This is a close-up image:
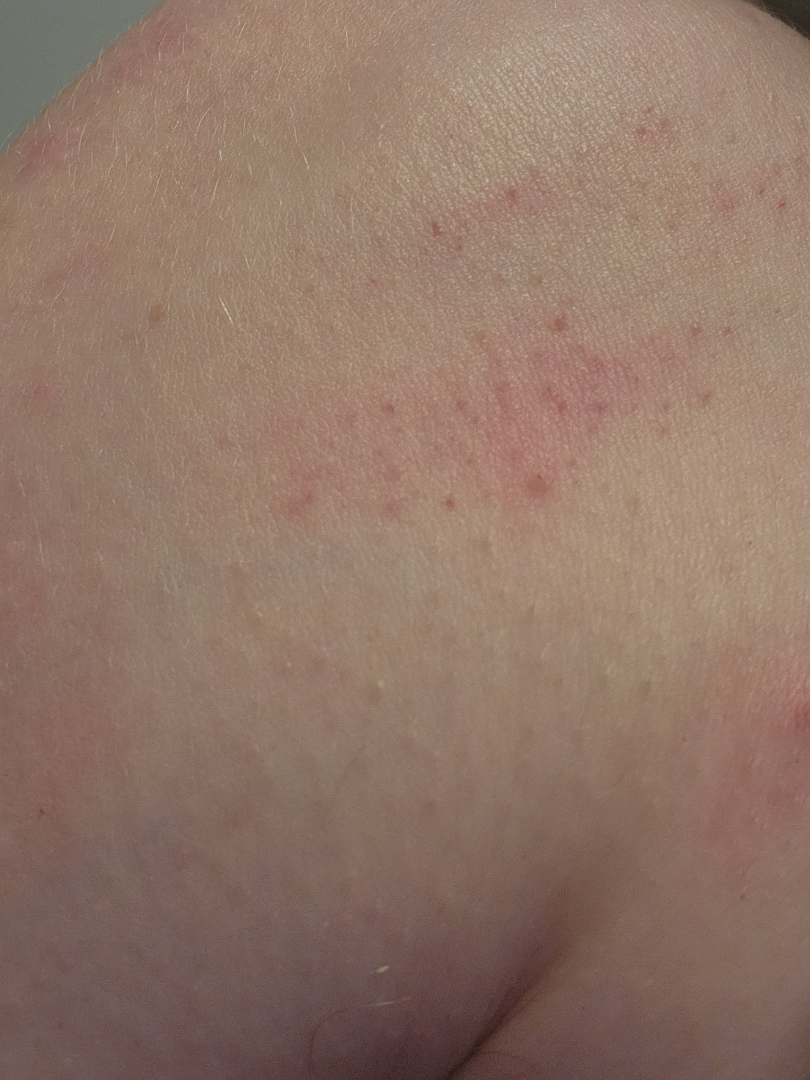• differential — a single dermatologist reviewed the case: the favored diagnosis is Folliculitis; possibly Keratosis pilaris; an alternative is Irritant Contact Dermatitis